This is a dermoscopic photograph of a skin lesion; a male subject, in their 50s.
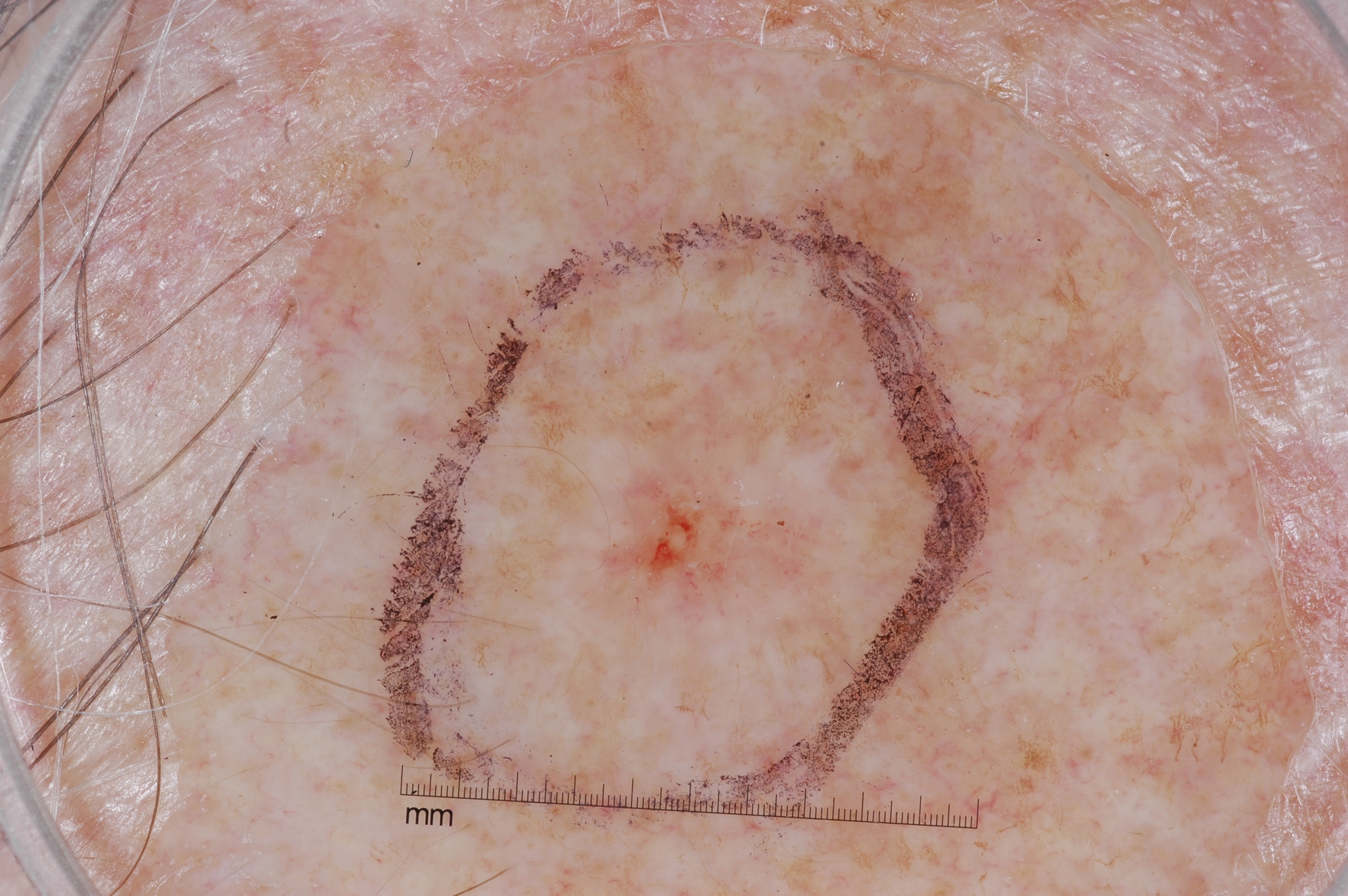With coordinates (x1, y1, x2, y2), the lesion occupies the region box(463, 242, 915, 775). Dermoscopy demonstrates no negative network, streaks, pigment network, or milia-like cysts. A moderately sized lesion. The diagnostic assessment was a seborrheic keratosis, a non-melanocytic (keratinocytic) lesion.